The contributor is female. The photograph is a close-up of the affected area.
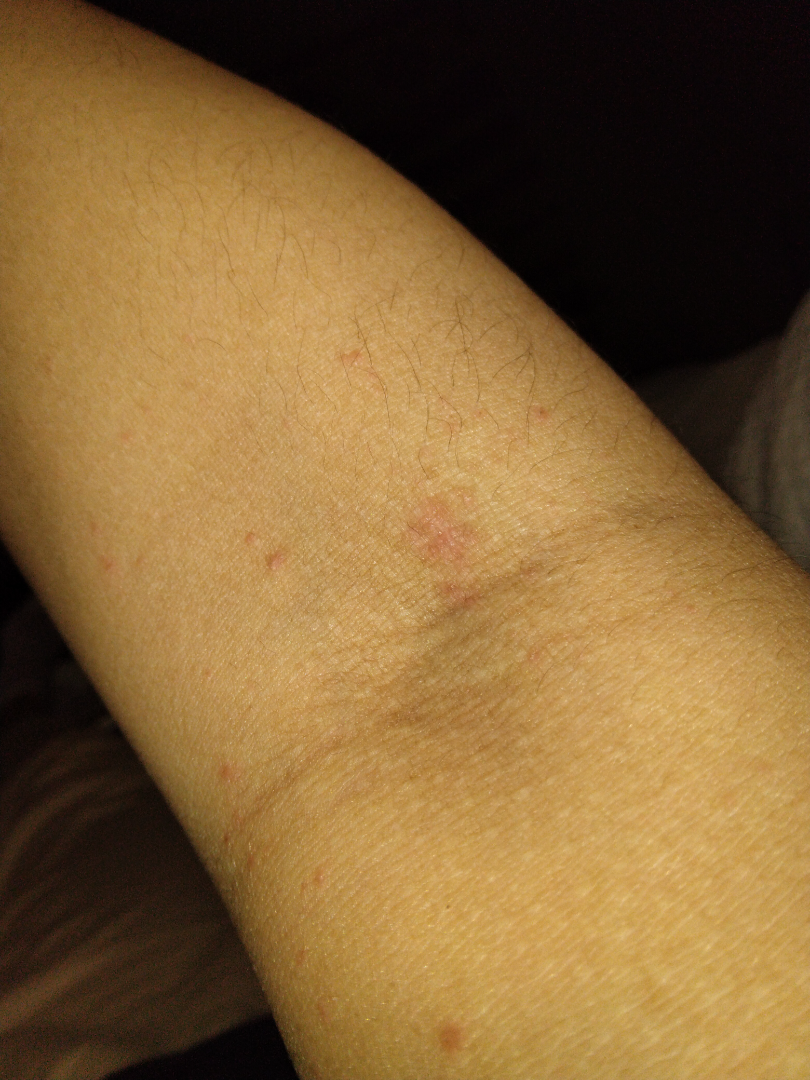The dermatologist could not determine a likely condition from the photograph alone.